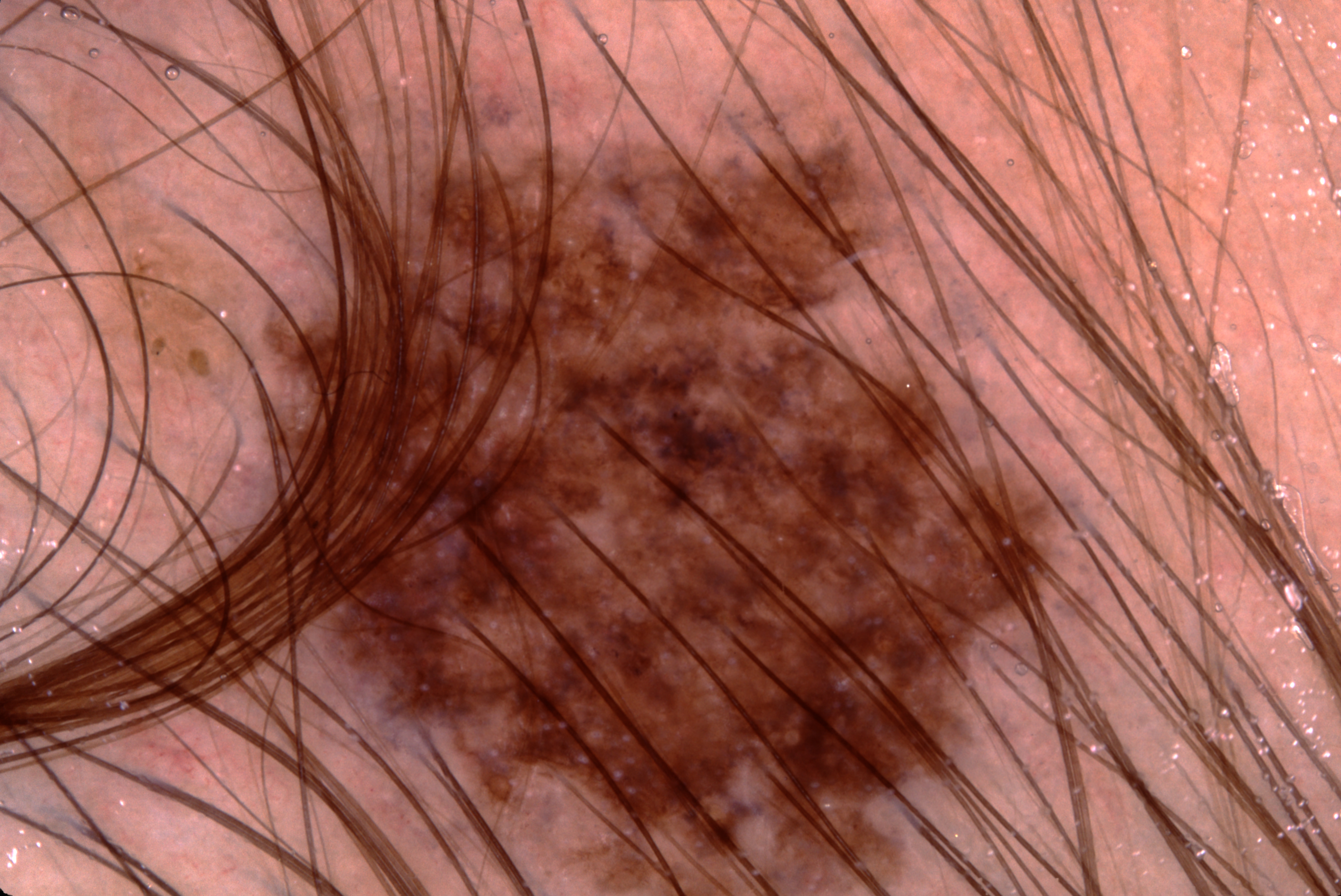image = dermoscopy; subject = female, aged 18 to 22; lesion extent = ~41% of the field; lesion location = 238/89/1079/892; dermoscopic pattern = pigment network and milia-like cysts; diagnosis = a melanocytic nevus.